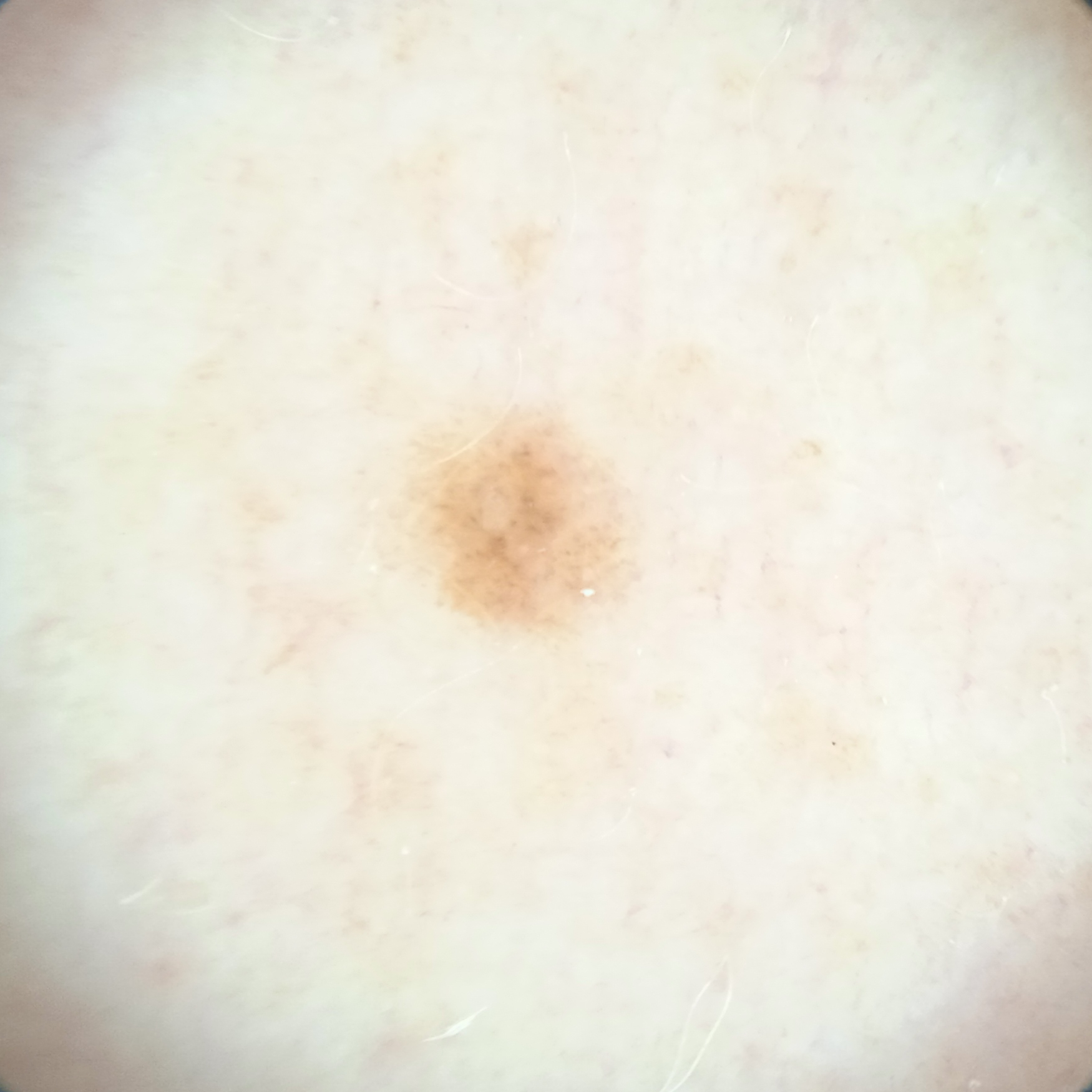A skin lesion imaged with a dermatoscope. Acquired for a research image collection, with no referral diagnosis. A female patient age 48. The lesion is located on an arm. The lesion measures approximately 2.7 mm. The dermatologists' assessment was a melanocytic nevus.